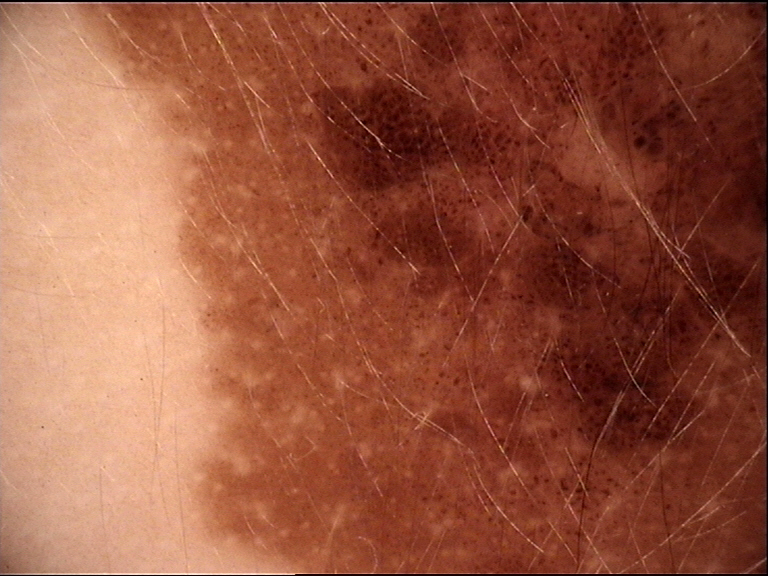{
  "diagnosis": {
    "name": "congenital junctional nevus",
    "code": "cjb",
    "malignancy": "benign",
    "super_class": "melanocytic",
    "confirmation": "expert consensus"
  }
}